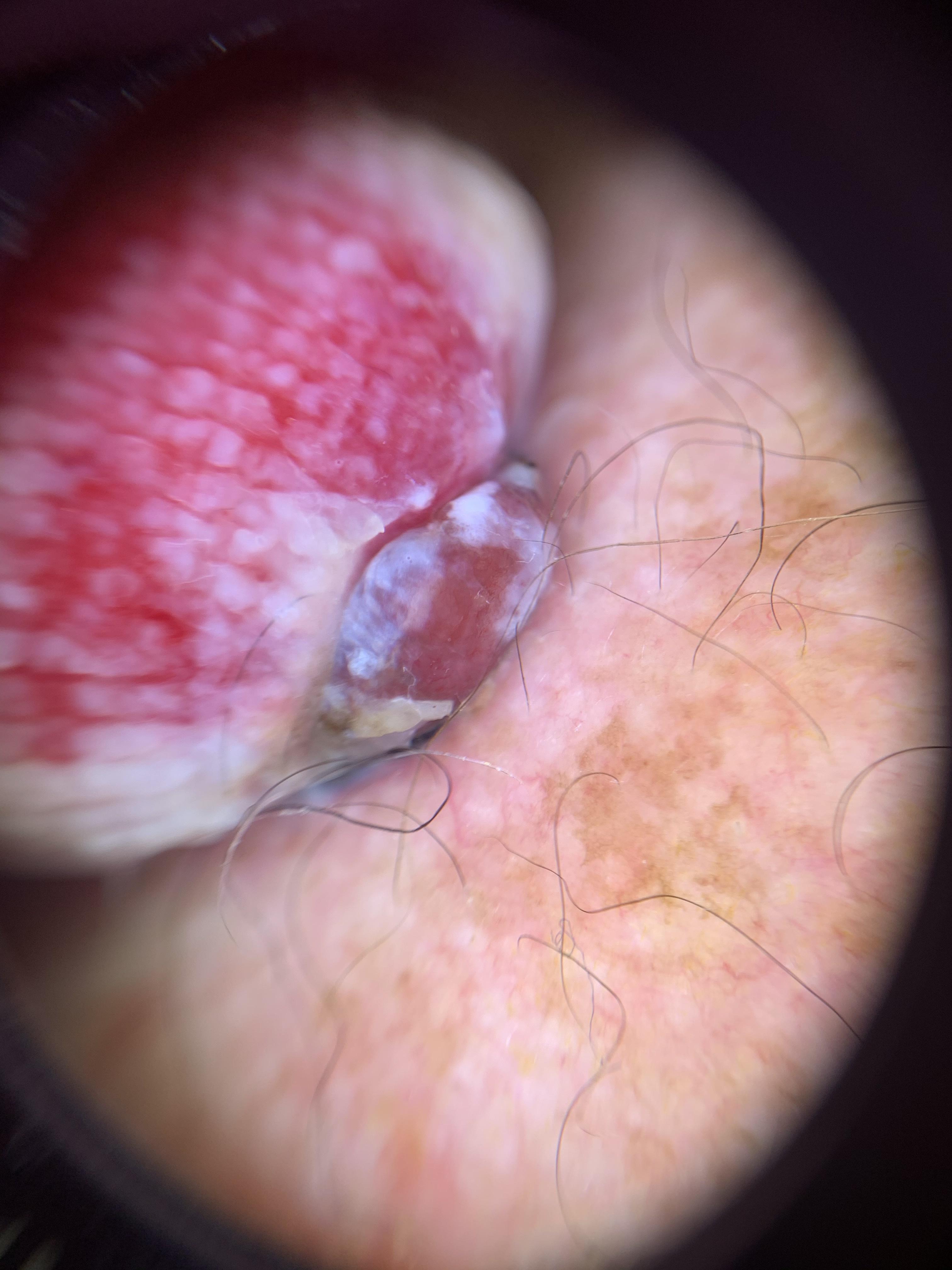A male subject in their mid-80s or older. FST II. The lesion involves an upper extremity. Histopathologically confirmed as a melanoma.